Fitzpatrick skin type II; lay reviewers estimated Monk Skin Tone 4 (US pool) or 3 (India pool) · the photograph is a close-up of the affected area · the patient is a male aged 18–29 · the patient indicates the lesion is raised or bumpy · no constitutional symptoms were reported · present for less than one week · symptoms reported: bothersome appearance and itching · the patient considered this a rash · the affected area is the arm.
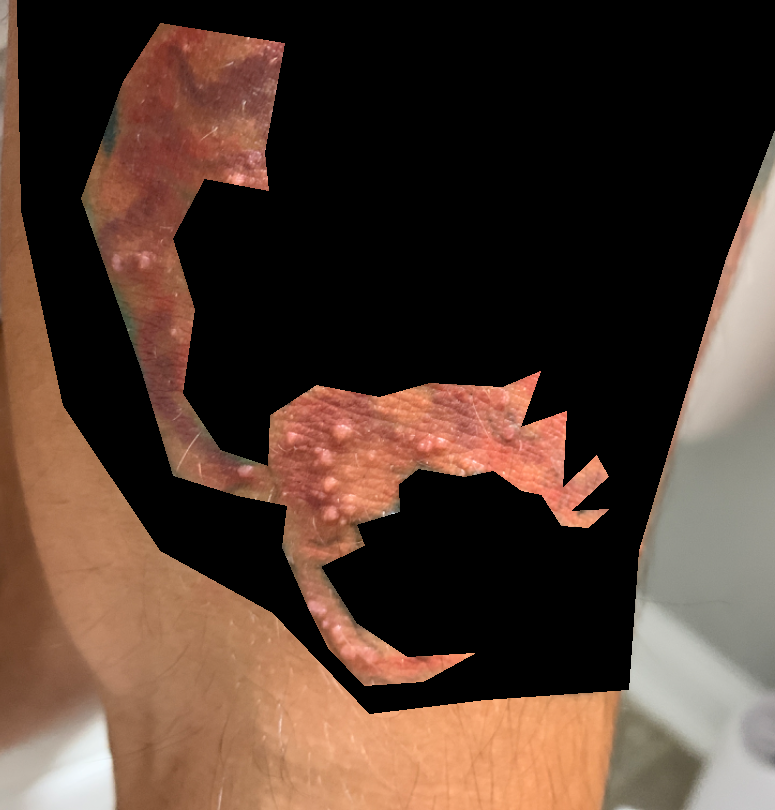• clinical impression — favoring Skin infection; possibly Foreign body reaction of the skin